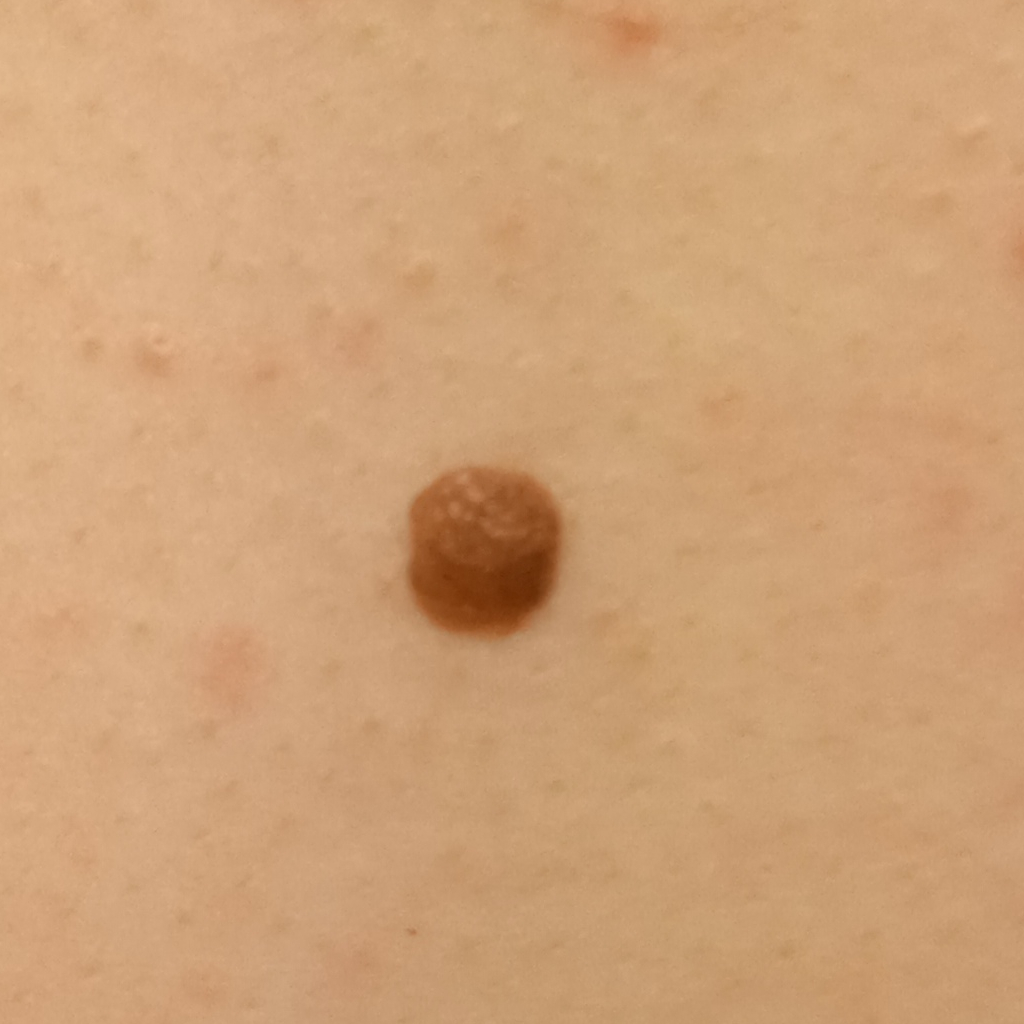A female patient age 26.
The lesion is on the back.
The lesion is about 5.6 mm across.
Dermatologist review favored a melanocytic nevus.